The contributor notes itching · no relevant systemic symptoms · the photograph was taken at a distance · the affected area is the arm · the lesion is described as raised or bumpy and fluid-filled · the patient considered this a rash — 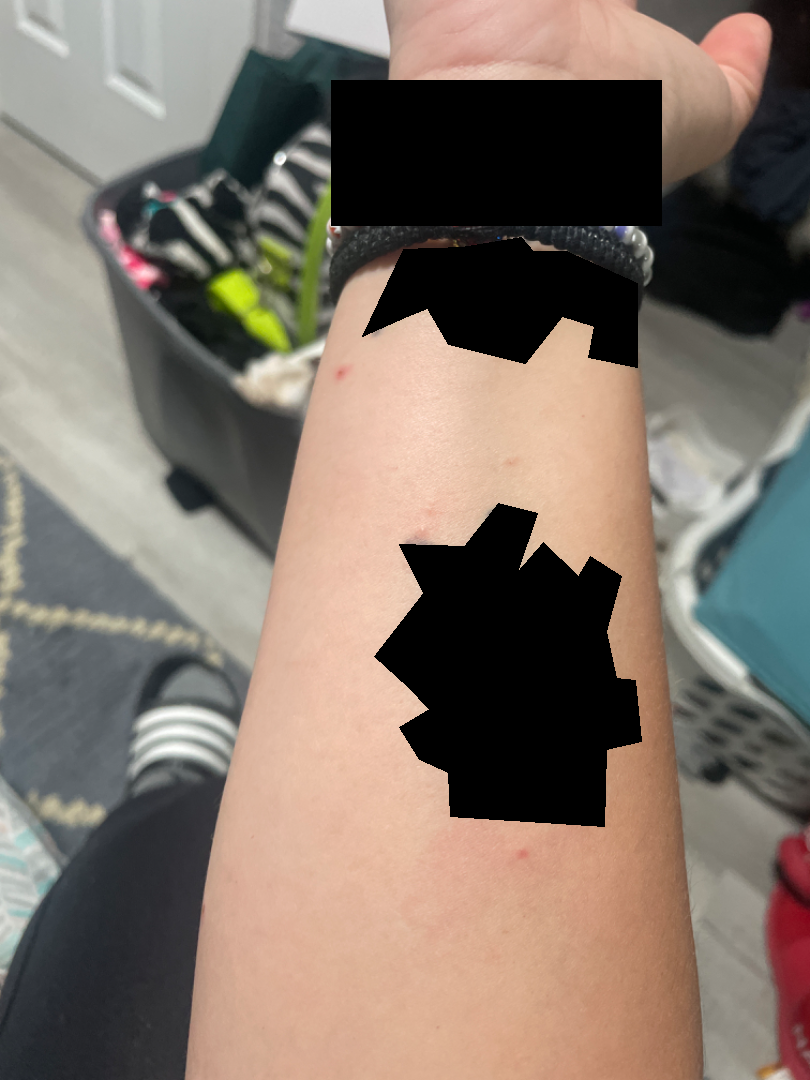The image was not sufficient for the reviewer to characterize the skin condition.